Texture is reported as raised or bumpy · no relevant systemic symptoms · the contributor notes the condition has been present for about one day · the affected area is the arm · an image taken at a distance · female subject, age 50–59 · Fitzpatrick phototype IV; lay graders estimated Monk skin tone scale 2 or 3 (two reviewer pools) · the lesion is associated with burning: 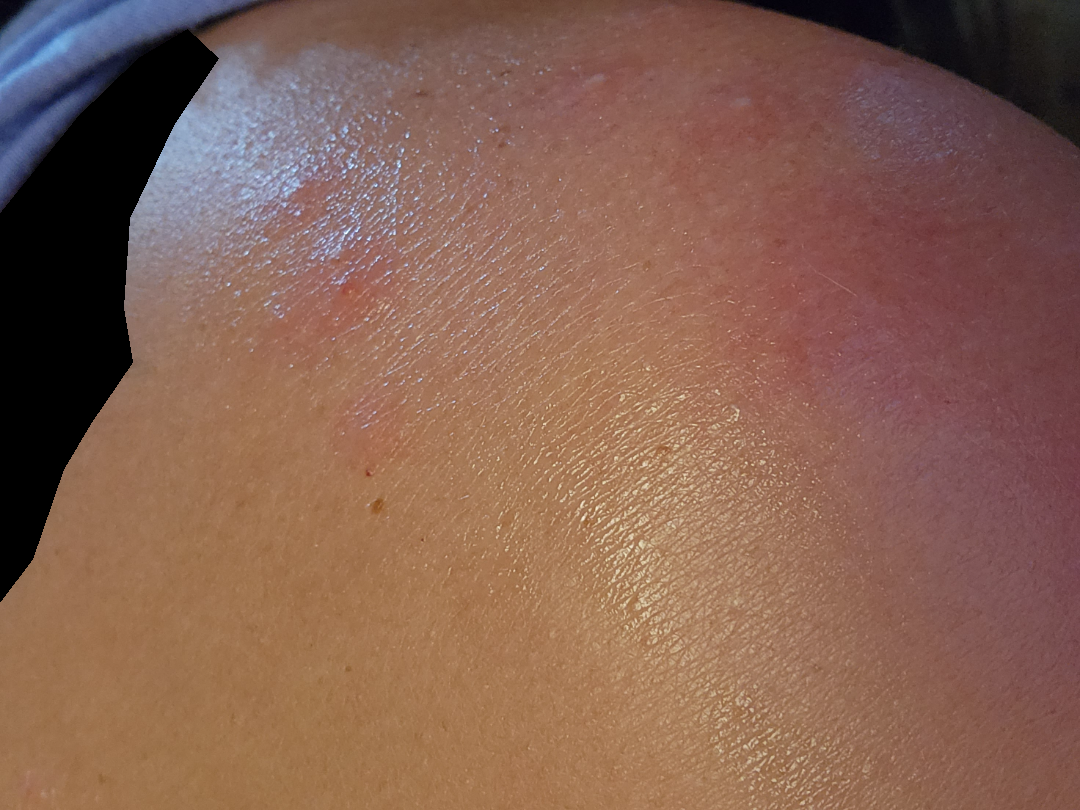Assessment: The reviewing dermatologist was unable to assign a differential diagnosis from the image.